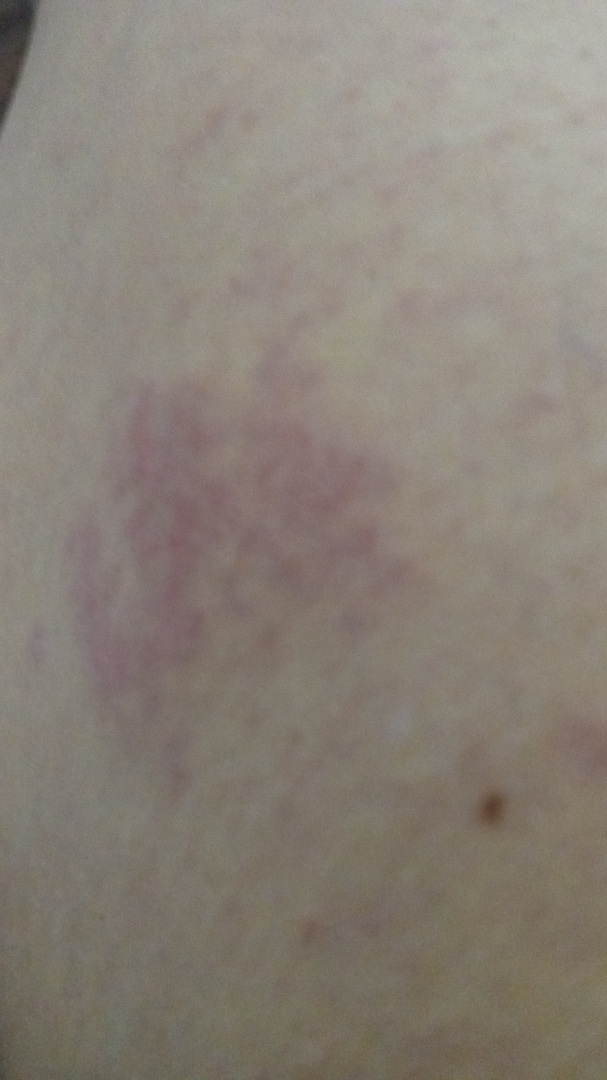<case>
<assessment>unable to determine</assessment>
<texture>raised or bumpy</texture>
<body_site>leg</body_site>
<shot_type>close-up</shot_type>
<duration>about one day</duration>
<symptoms>itching, bothersome appearance</symptoms>
<patient_category>a rash</patient_category>
</case>